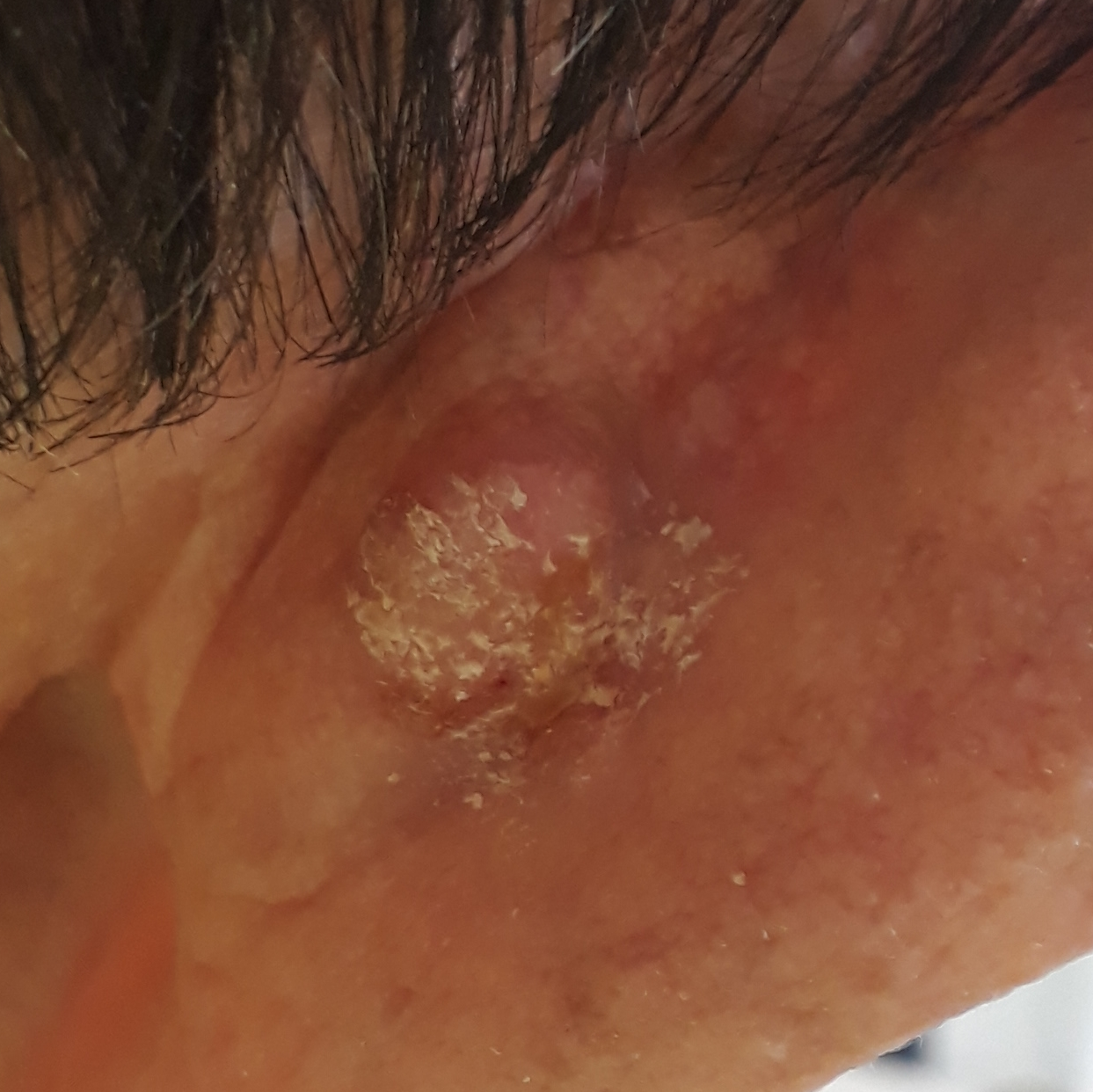Pathology: Biopsy-confirmed as a squamous cell carcinoma.